A dermoscopic close-up of a skin lesion: 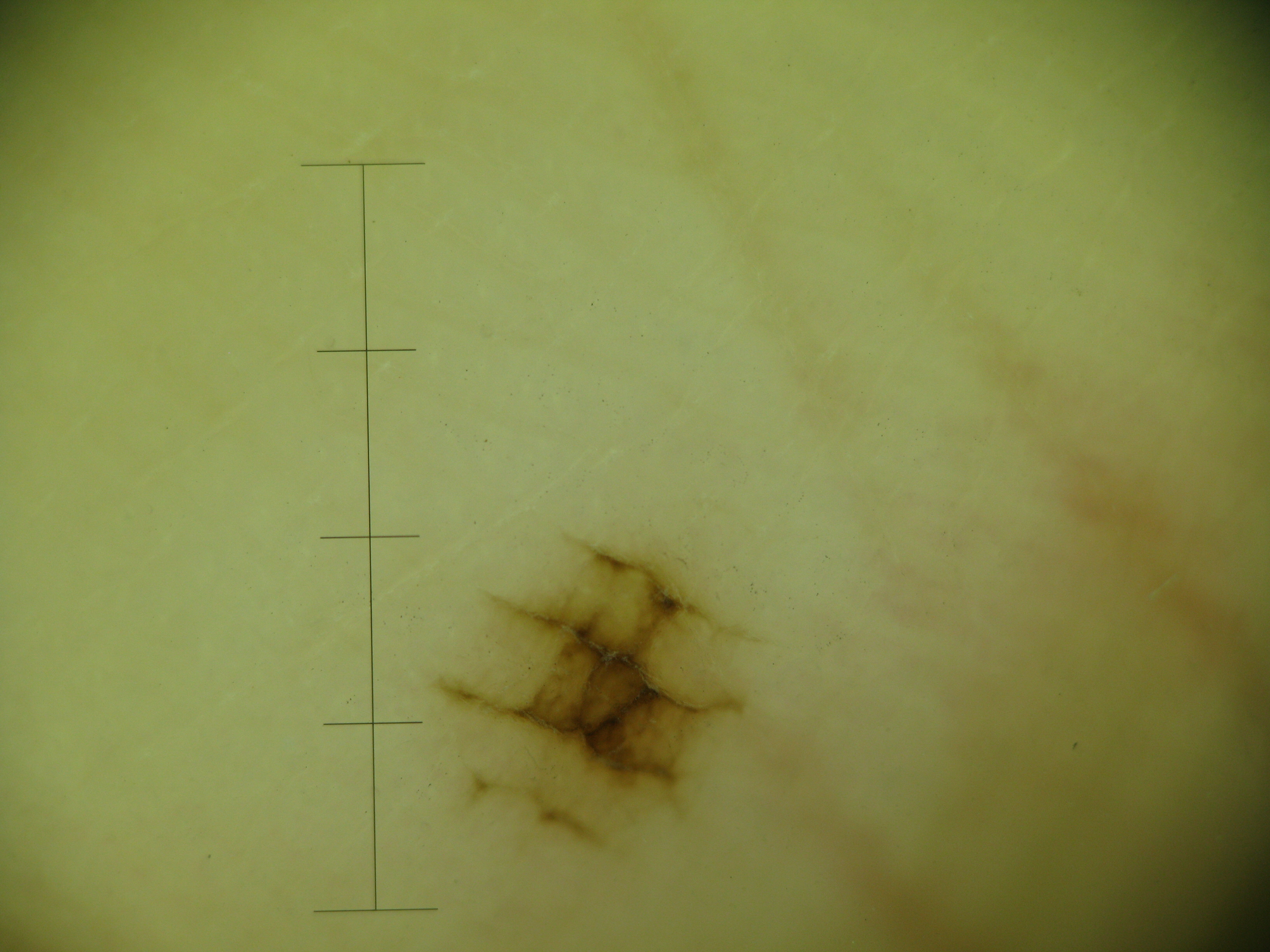Q: What is this lesion?
A: acral junctional nevus (expert consensus)